The patient was assessed as Fitzpatrick phototype II. The chart records a previous melanoma. A dermoscopy image of a single skin lesion. A male subject in their mid-80s or older — 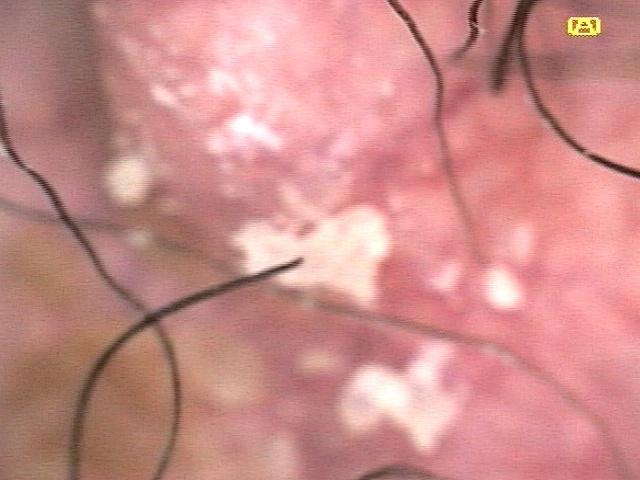The lesion involves the head or neck. Expert review favored a solar or actinic keratosis.